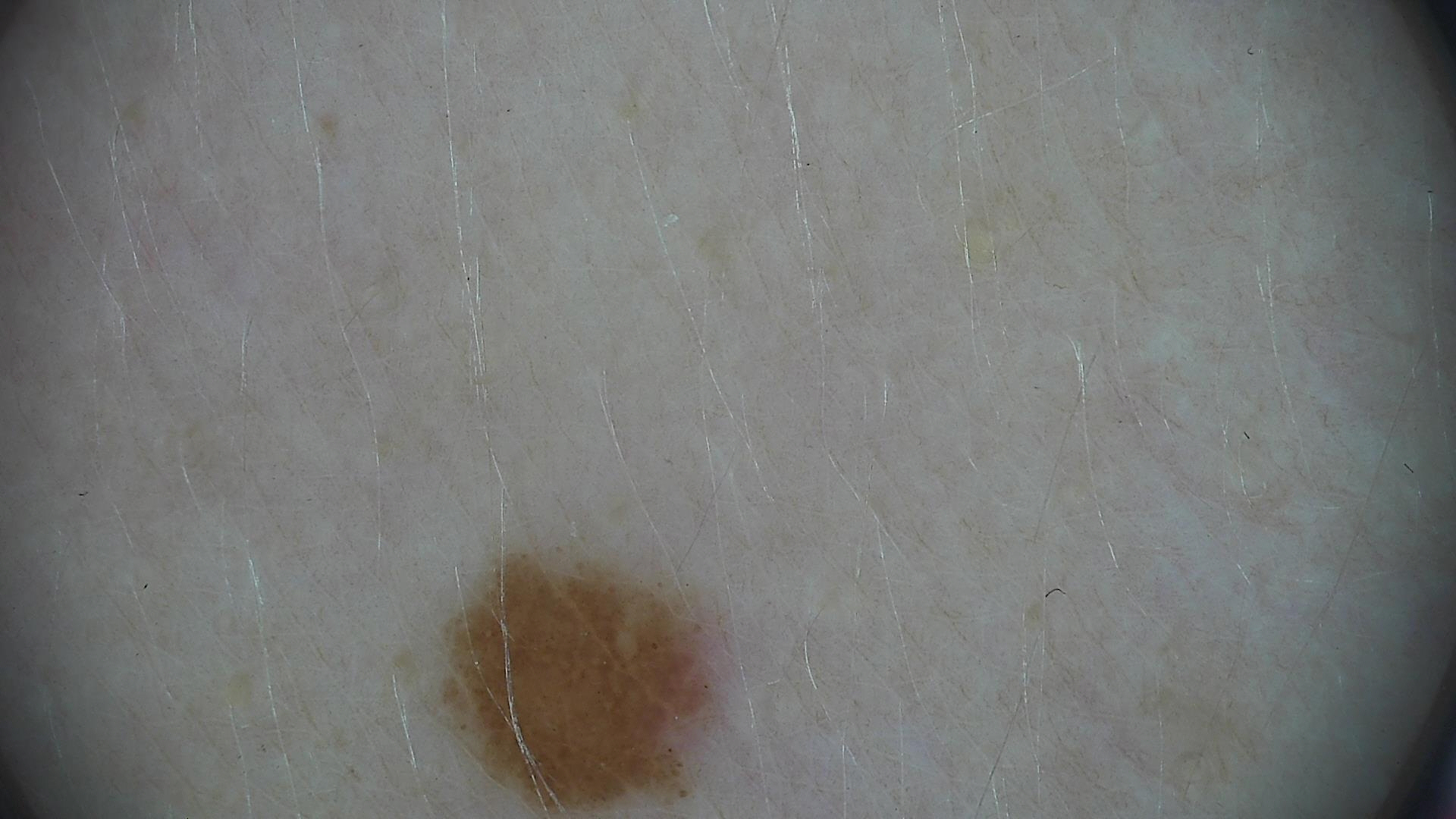* image type · dermoscopy
* label · dysplastic junctional nevus (expert consensus)